Located on the head or neck and back of the torso · the photo was captured at a distance:
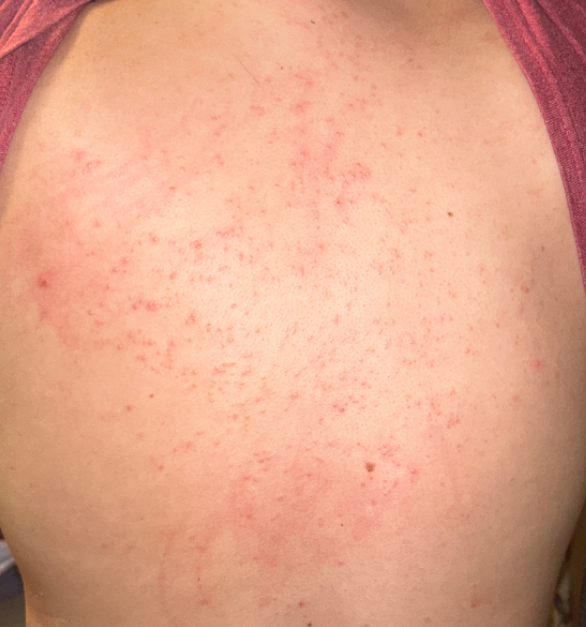differential diagnosis = favoring Folliculitis; possibly Acne.